A female patient 50 years old; a clinical photograph of a skin lesion; a moderate number of moles by the patient's own estimate; acquired for a research image collection, with no referral diagnosis; the patient reports a personal history of skin cancer; the patient says their skin reddens with sun exposure:
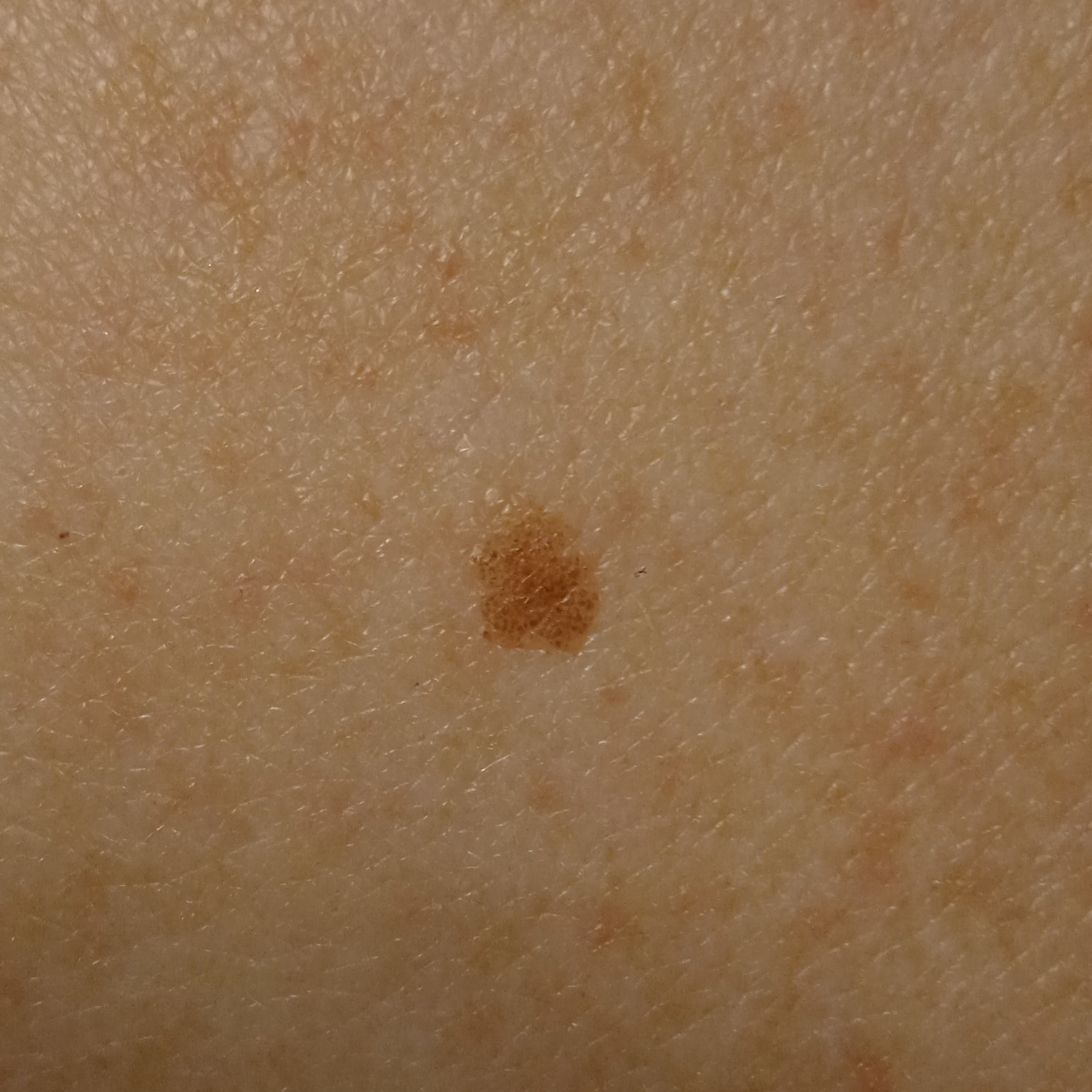| feature | finding |
|---|---|
| diameter | 5.1 mm |
| diagnostic label | melanocytic nevus (dermatologist consensus) |